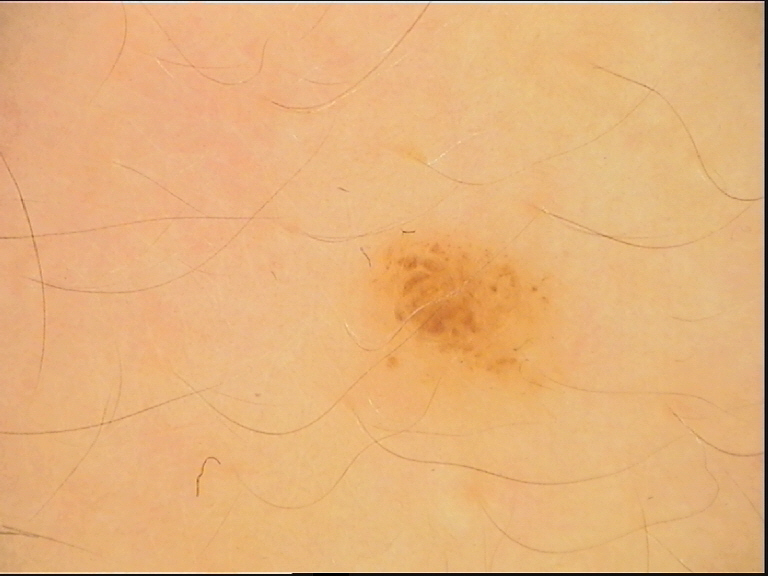label = dysplastic junctional nevus (expert consensus)